The patient considered this a rash. The affected area is the leg. The patient is 50–59, female. The lesion is associated with pain, enlargement, itching and burning. An image taken at an angle. Texture is reported as fluid-filled and raised or bumpy: 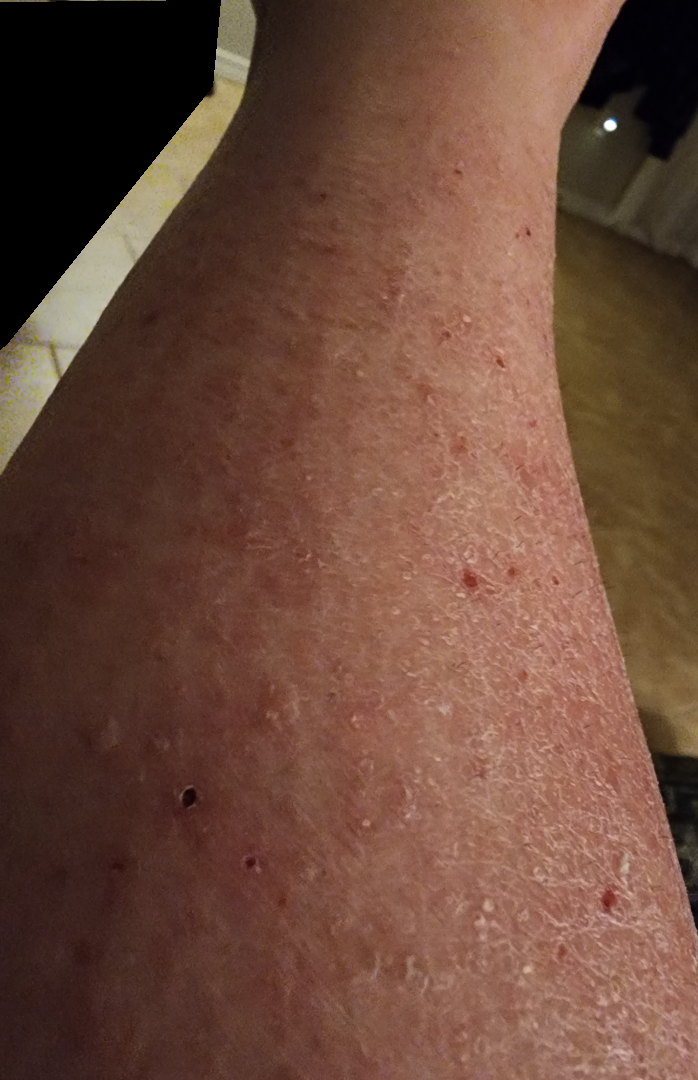The leading impression is Eczema; an alternative is Xerosis; less probable is Stasis Dermatitis.